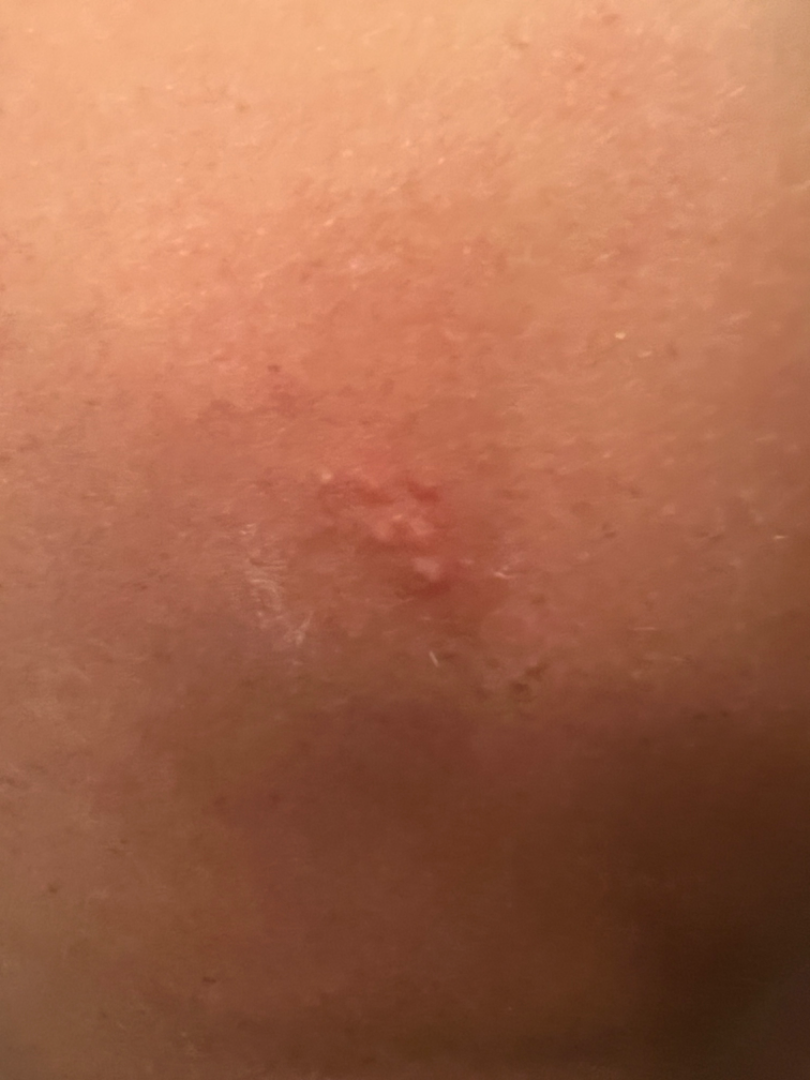Patient information:
The leg is involved. The photograph is a close-up of the affected area.
Review:
The reviewing clinician's impression was: Acne, Molluscum Contagiosum and Herpes Simplex were considered with similar weight.